The lesion involves the back of the hand. The photo was captured at an angle. The patient is female: 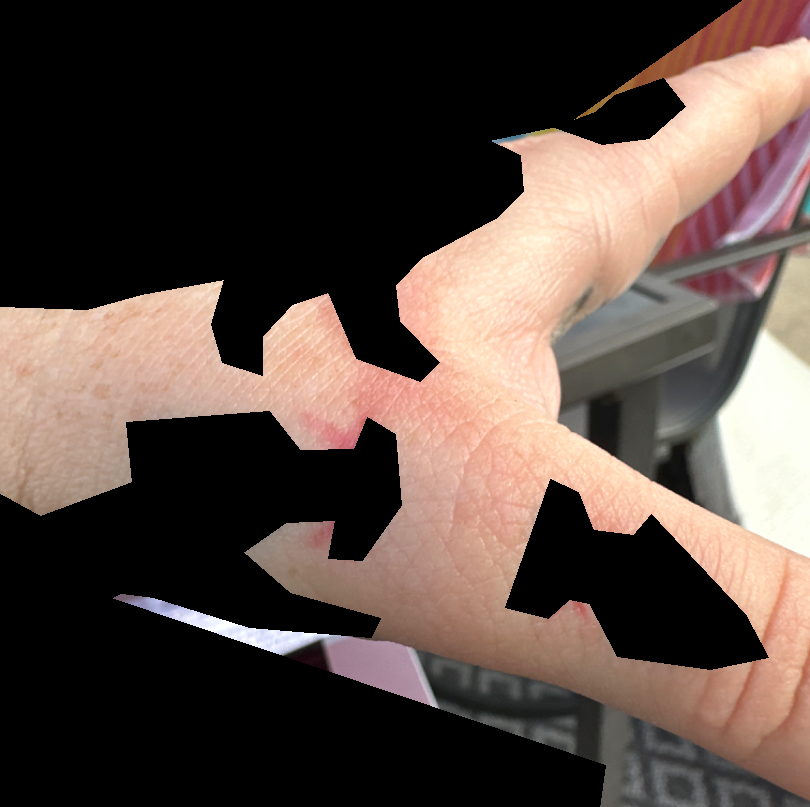Assessment: On independent review by the dermatologists: most consistent with Eczema; also raised was Allergic Contact Dermatitis; the differential also includes Irritant Contact Dermatitis.